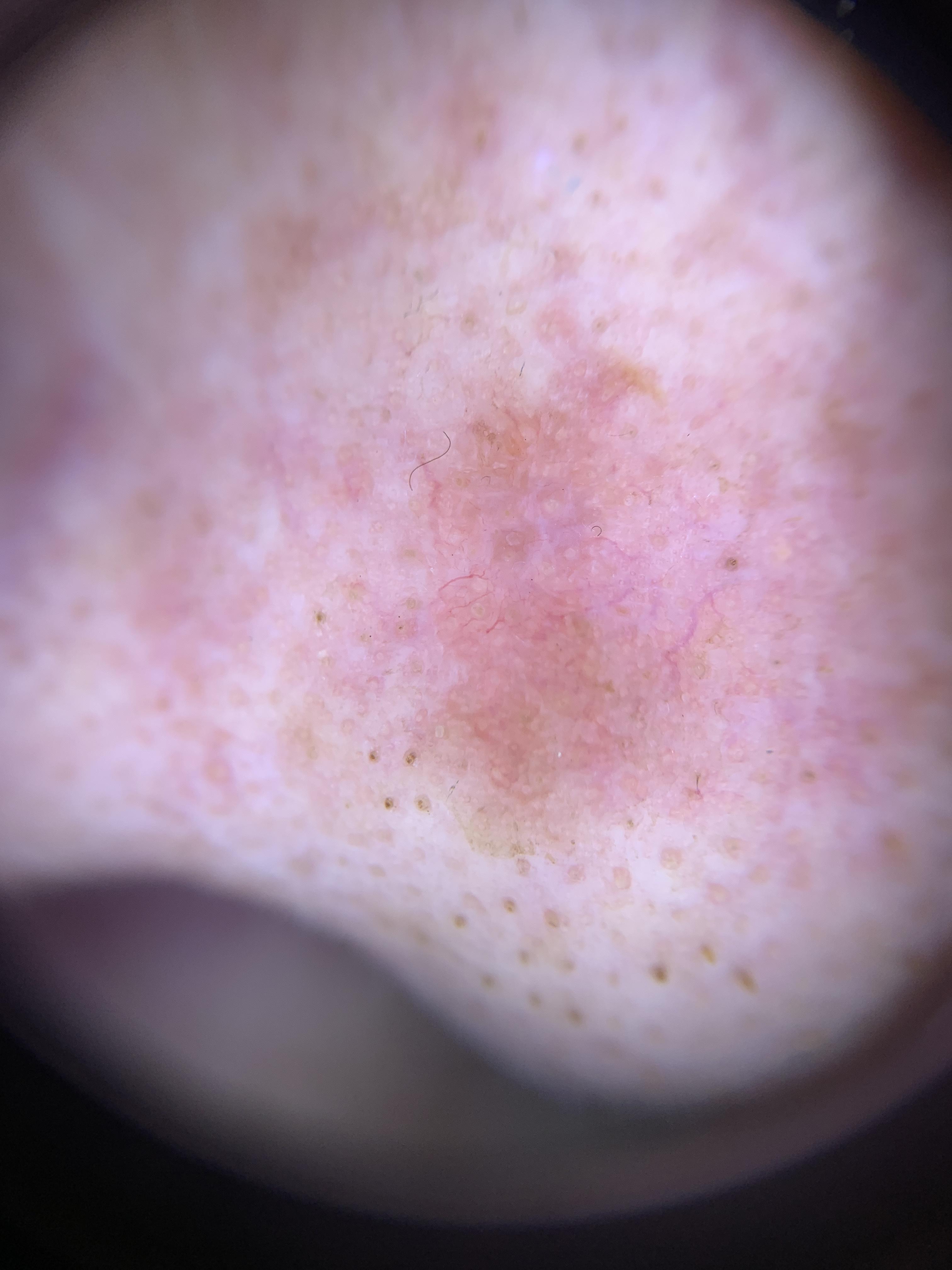skin type: II
image type: contact-polarized dermoscopy
diagnostic label: Basal cell carcinoma (biopsy-proven)